The photograph is a close-up of the affected area; female subject, age 18–29 — 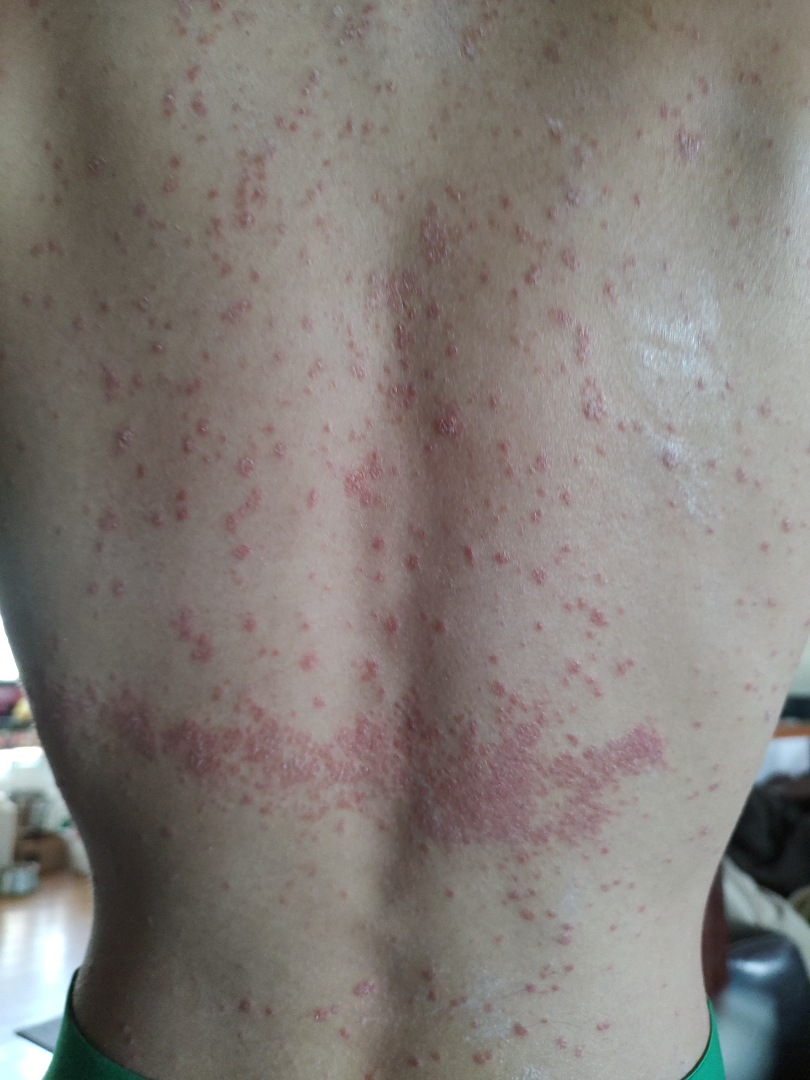On photographic review: the primary impression is Psoriasis; an alternative is Drug Rash.